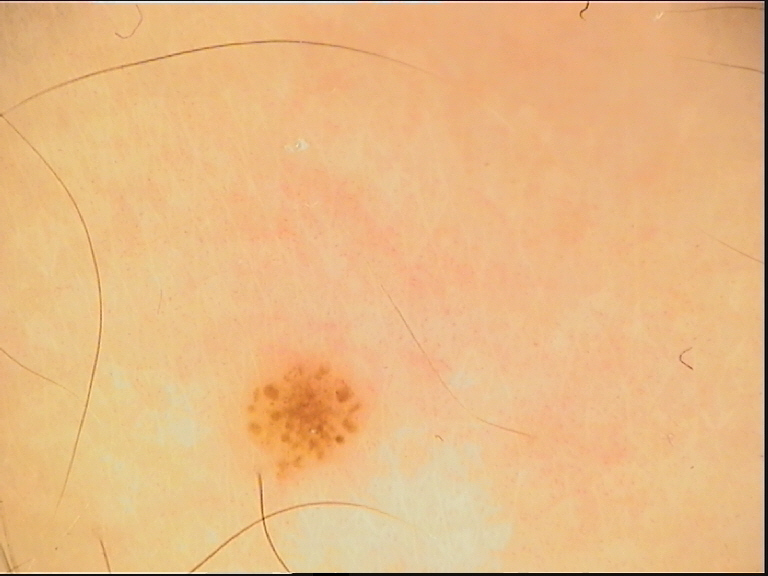diagnosis:
  name: dysplastic junctional nevus
  code: jd
  malignancy: benign
  super_class: melanocytic
  confirmation: expert consensus